A dermoscopic image of a skin lesion.
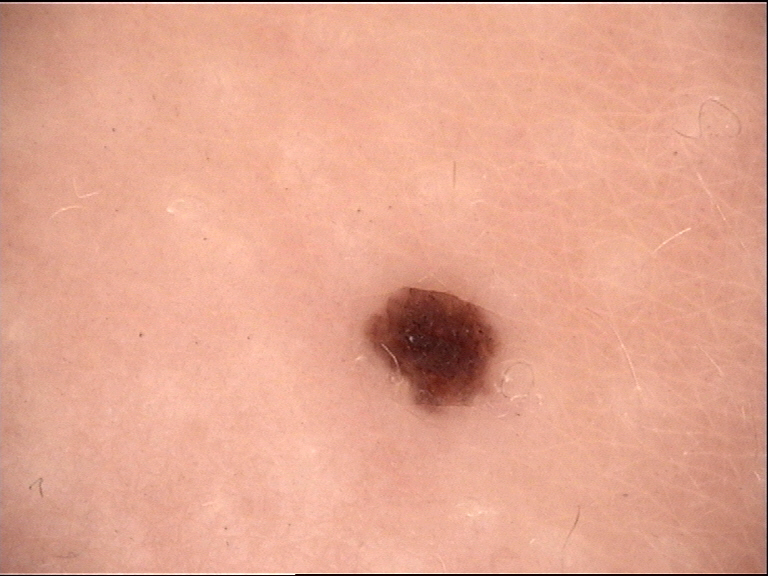{
  "diagnosis": {
    "name": "compound nevus",
    "code": "cb",
    "malignancy": "benign",
    "super_class": "melanocytic",
    "confirmation": "expert consensus"
  }
}